A dermoscopic image of a skin lesion.
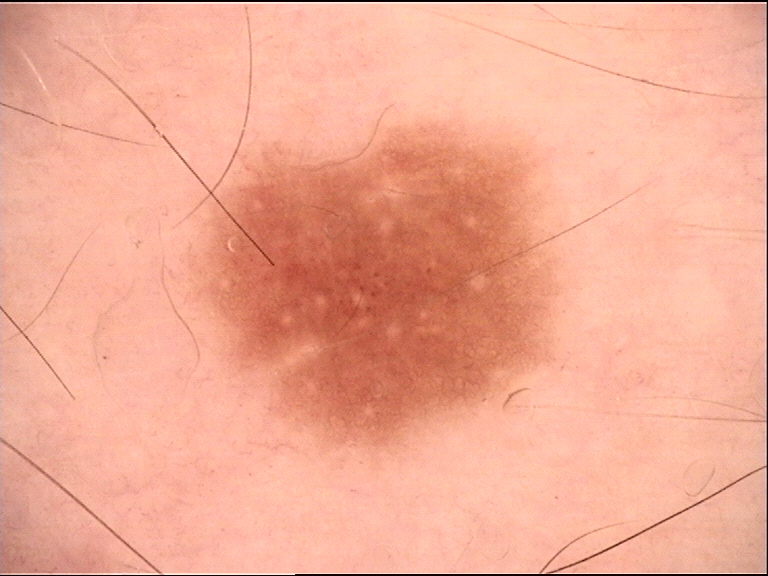<case>
  <diagnosis>
    <name>dysplastic junctional nevus</name>
    <code>jd</code>
    <malignancy>benign</malignancy>
    <super_class>melanocytic</super_class>
    <confirmation>expert consensus</confirmation>
  </diagnosis>
</case>